The photograph is a close-up of the affected area — 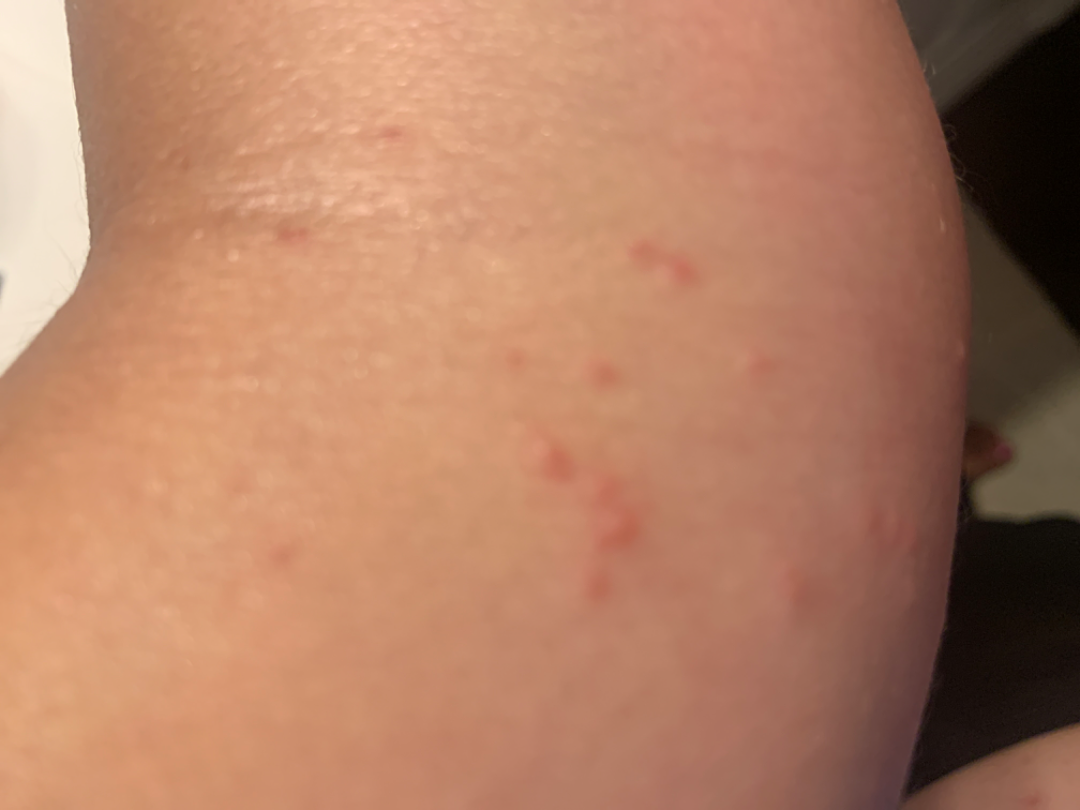The image was not sufficient for the reviewer to characterize the skin condition.